A clinical photograph of a skin lesion; a subject in their mid-40s:
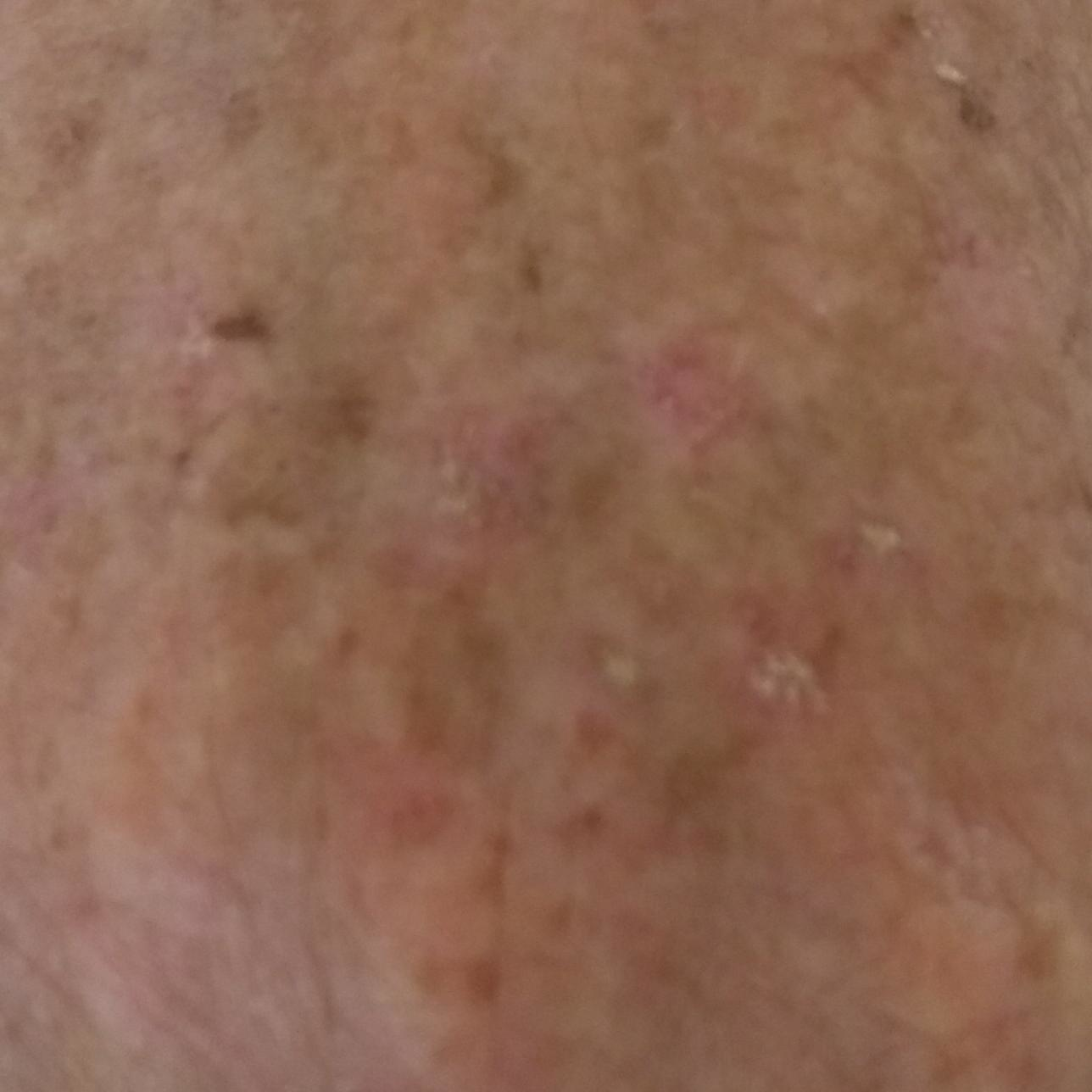The lesion is on a hand. The patient describes that the lesion is elevated and itches. The clinical impression was an actinic keratosis.